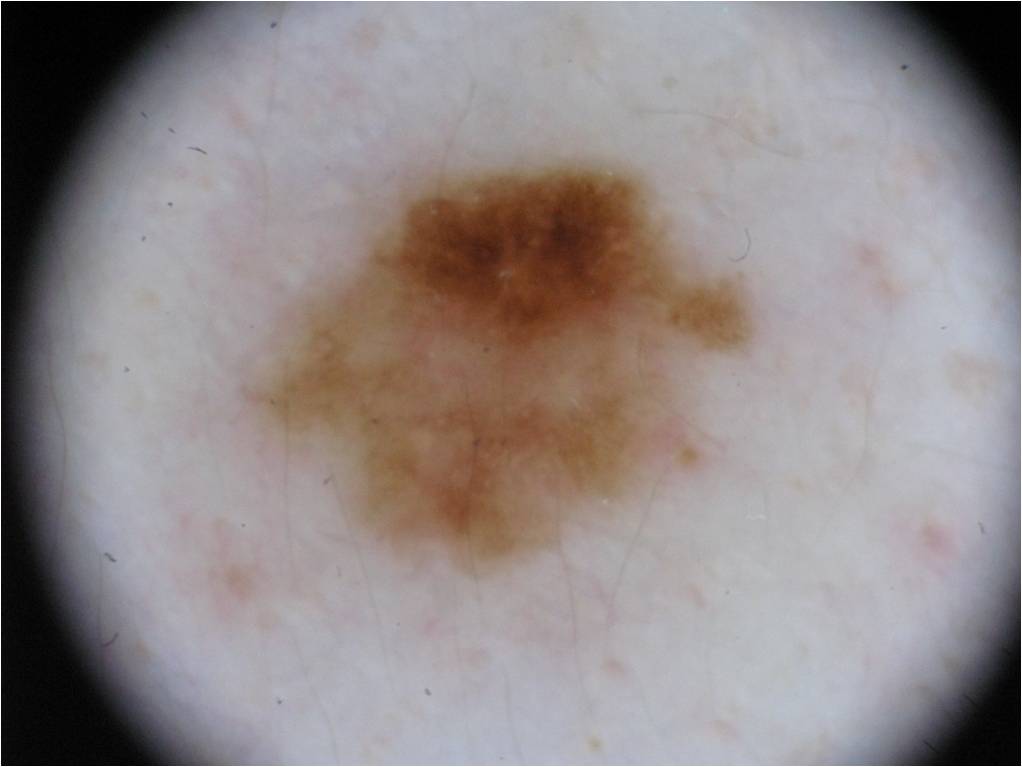A female subject aged 33-37. A dermoscopic view of a skin lesion. Dermoscopically, the lesion shows milia-like cysts, with no globules, negative network, pigment network, or streaks. In (x1, y1, x2, y2) order, the lesion is bounded by (244, 154, 752, 573). Consistent with a melanocytic nevus, a benign lesion.